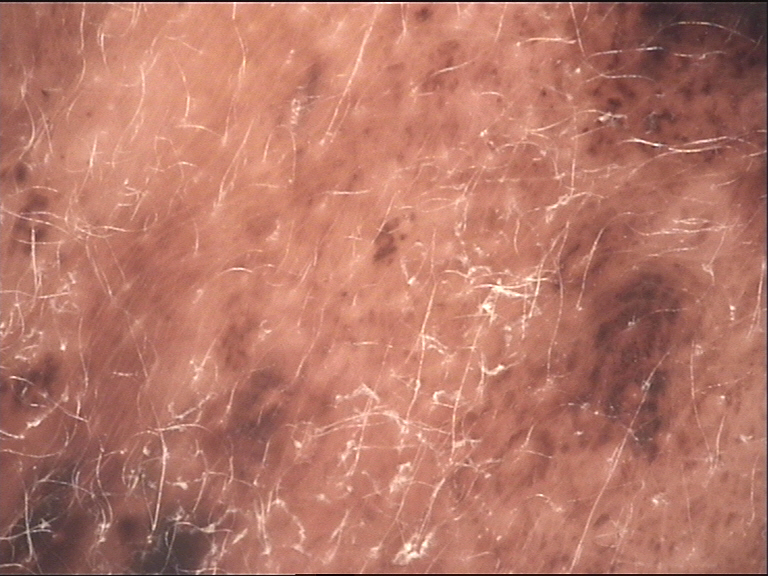imaging: dermatoscopy
category: banal
diagnostic label: congenital compound nevus (expert consensus)